The affected area is the leg, the contributor is a female aged 50–59, this image was taken at an angle: 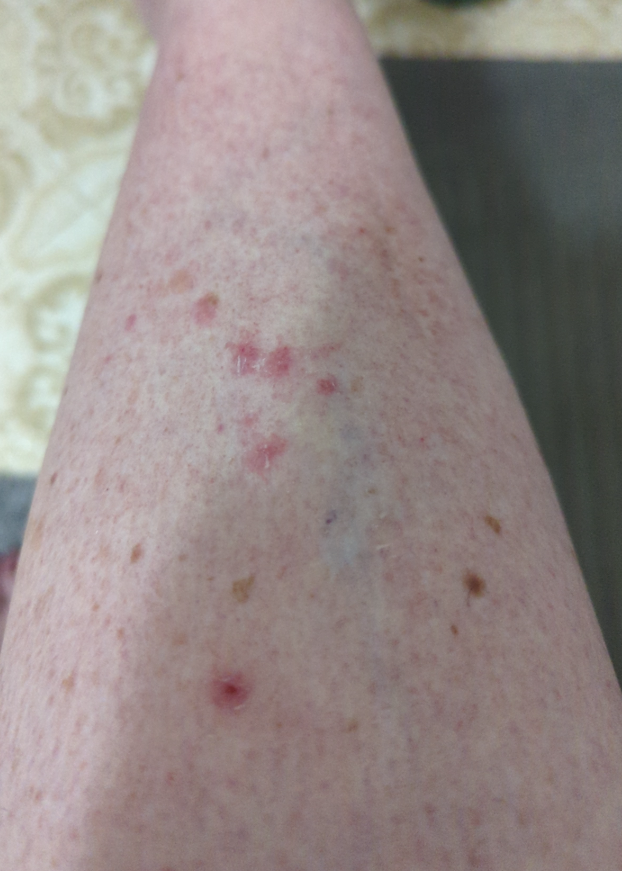dermatologist impression = one reviewing dermatologist: the differential includes Pigmented purpuric eruption, Stasis Dermatitis and Eczema, with no clear leading consideration